No associated systemic symptoms reported; close-up view; female subject, age 50–59; the contributor notes the lesion is raised or bumpy and rough or flaky; located on the head or neck; the contributor notes burning, pain, itching and bothersome appearance; self-categorized by the patient as a rash — 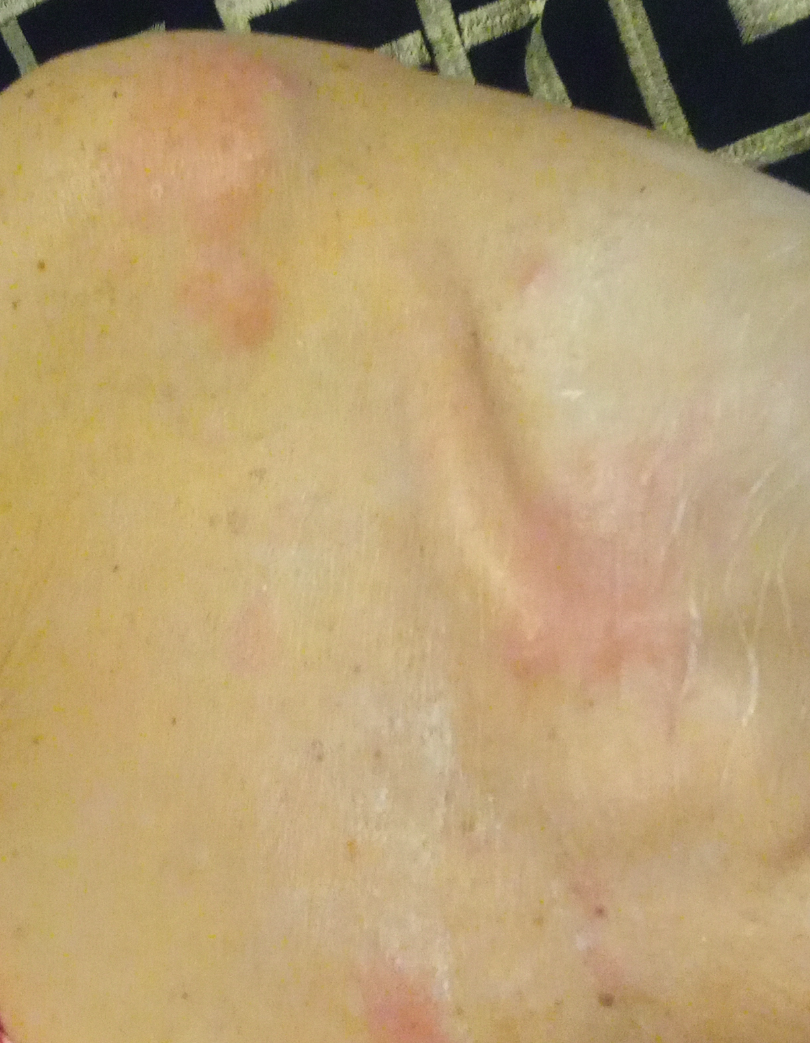The skin condition could not be confidently assessed from this image.